The contributor reports the lesion is rough or flaky · skin tone: Fitzpatrick phototype III · this image was taken at a distance · the head or neck is involved · the contributor reports bothersome appearance, pain and burning · the patient considered this a rash.
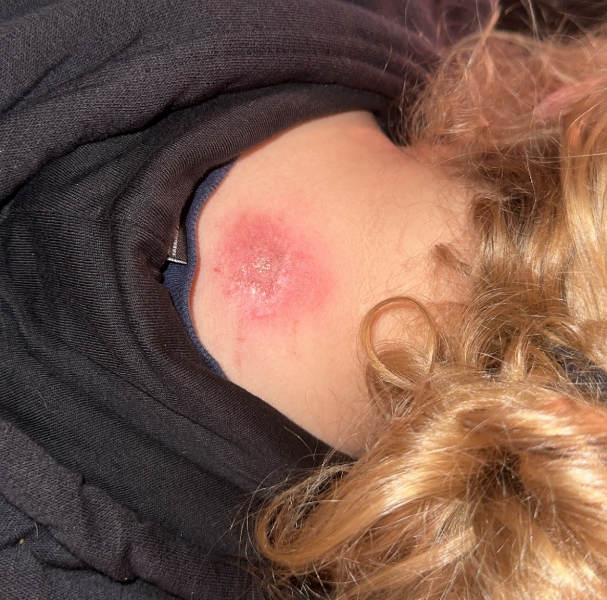On dermatologist assessment of the image: Eczema (leading); Irritant Contact Dermatitis (considered).